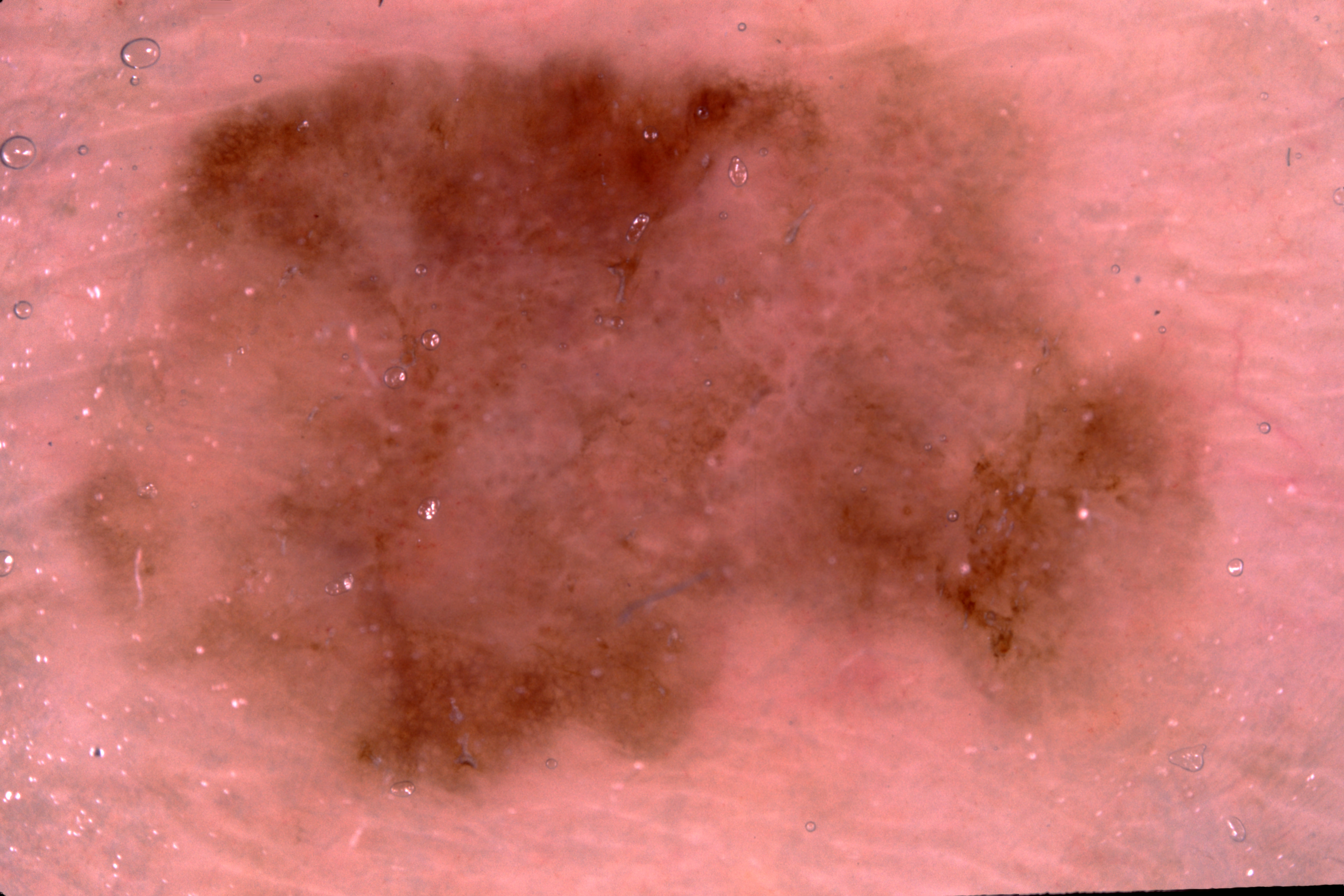Notes:
* imaging · dermoscopy
* subject · male, in their mid- to late 80s or older
* extent · large
* lesion location · (53, 31, 1210, 809)
* features · negative network and pigment network; absent: milia-like cysts and streaks
* diagnostic label · a melanocytic nevus, a benign lesion